Symptoms reported: itching, the lesion is described as raised or bumpy, present for one to four weeks, the affected area is the arm, the photo was captured at an angle, Fitzpatrick skin type III — 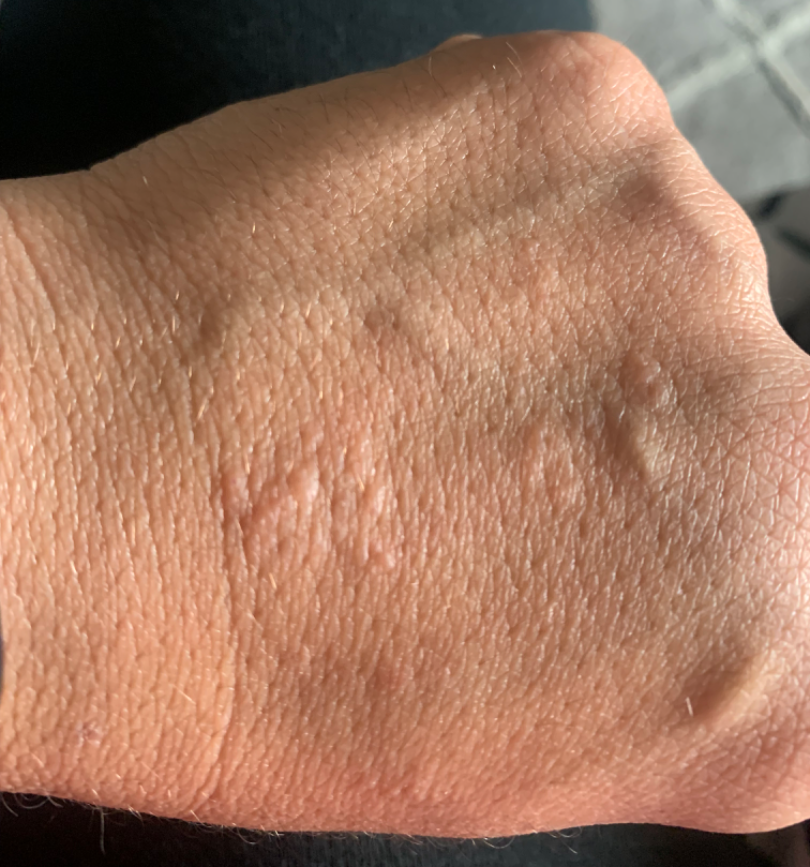Eczema (possible); Allergic Contact Dermatitis (possible); Psoriasis (less likely).